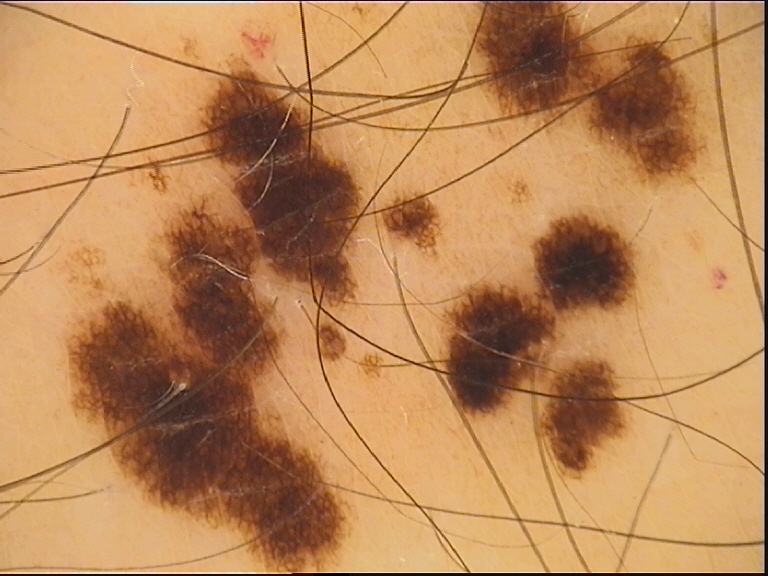modality=dermoscopy
diagnosis=dysplastic junctional nevus (expert consensus)